A dermoscopy image of a single skin lesion.
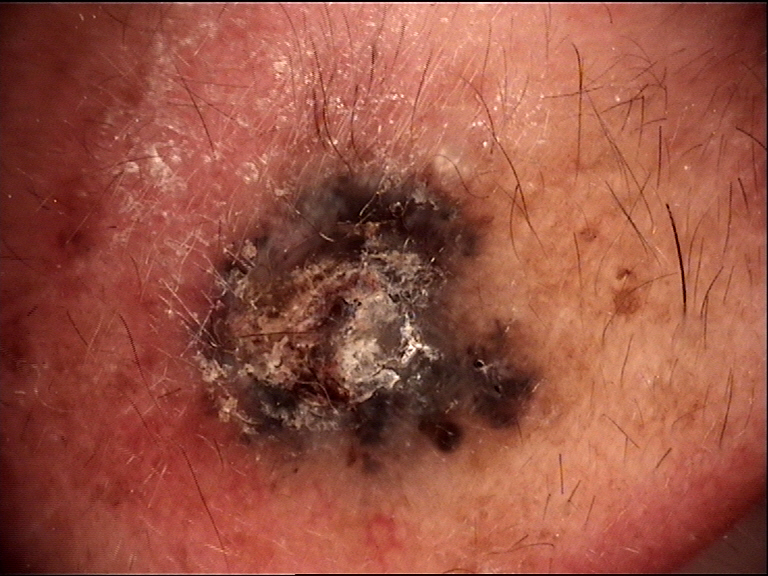This is a keratinocytic lesion. Histopathologically confirmed as a basal cell carcinoma.